A dermatoscopic image of a skin lesion:
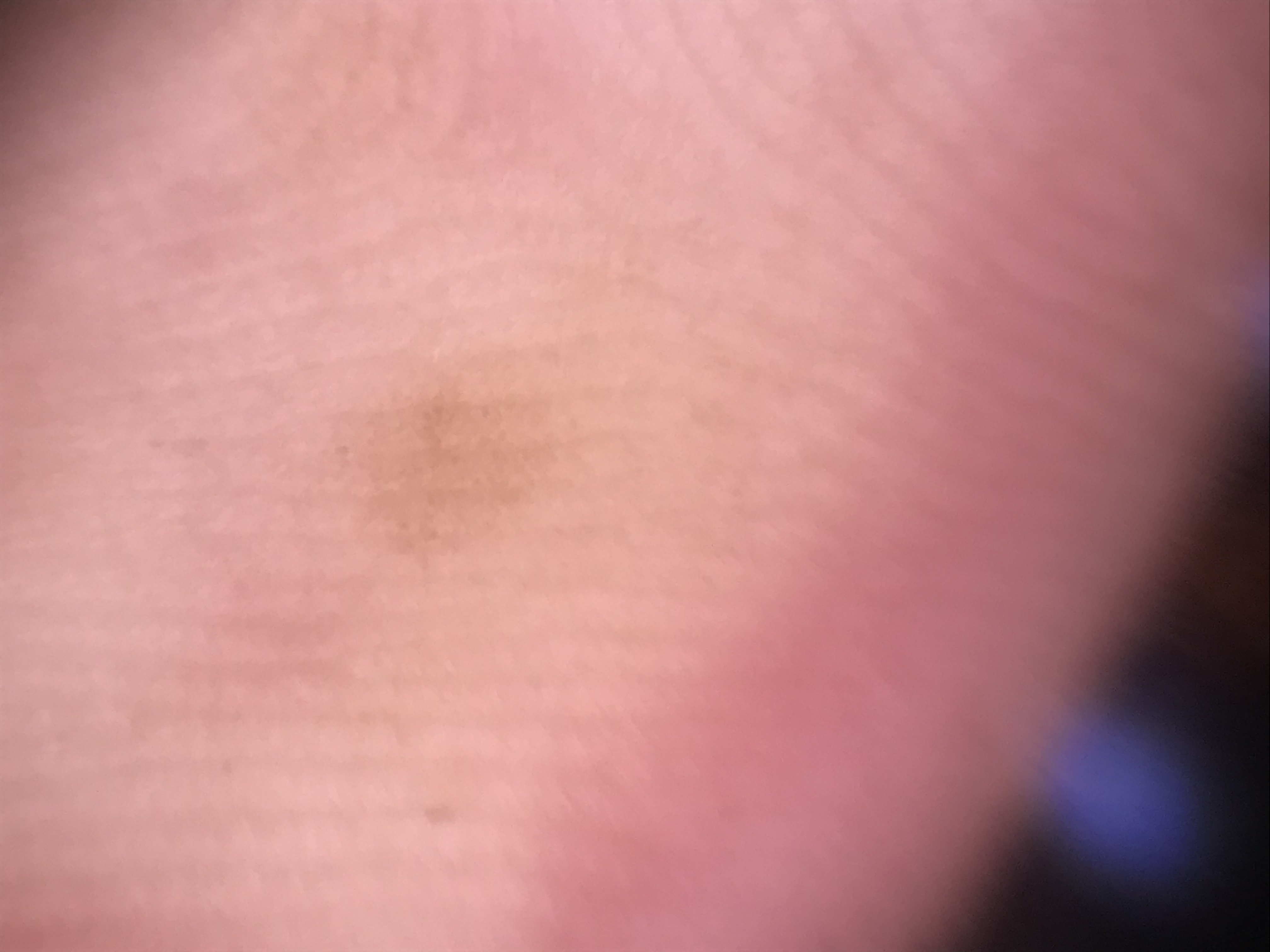label=acral junctional nevus (expert consensus).